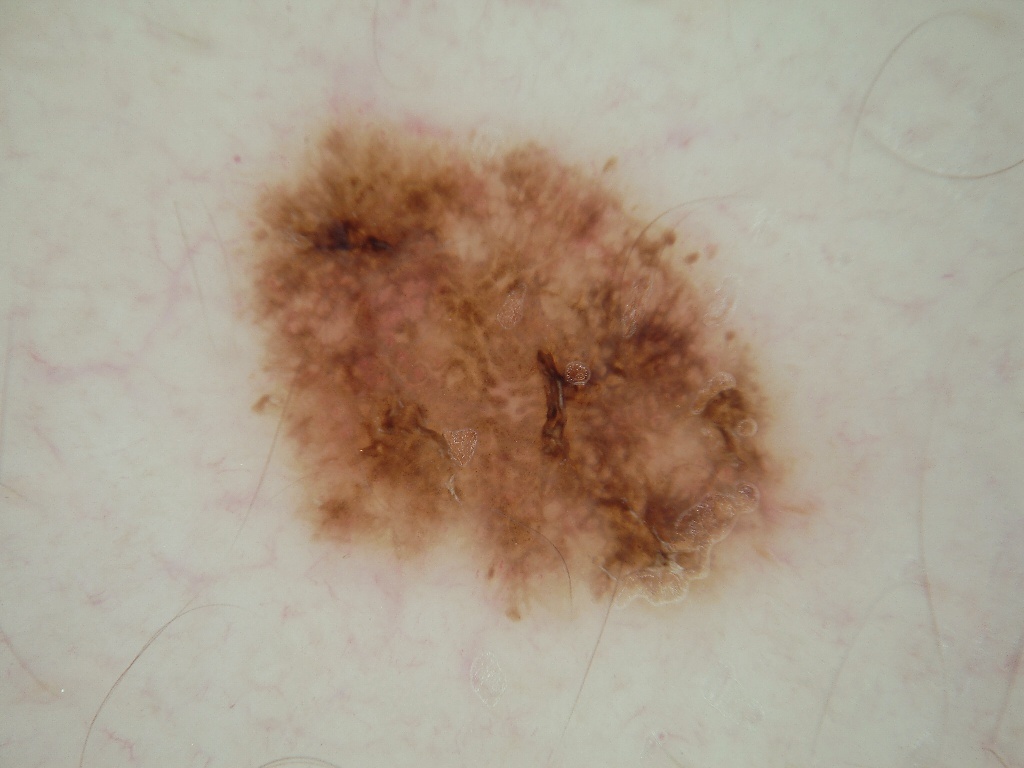Findings:
• image type — dermoscopy of a skin lesion
• subject — male, approximately 35 years of age
• location — left=224, top=96, right=868, bottom=621
• features — negative network, globules, and pigment network; absent: streaks and milia-like cysts
• diagnostic label — a melanocytic nevus, a benign lesion